Close-up view; the patient indicates the lesion is raised or bumpy; self-categorized by the patient as a rash; the contributor is a female aged 18–29; symptoms reported: pain, itching, darkening and bothersome appearance; no constitutional symptoms were reported; the condition has been present for one to four weeks; the affected area is the leg: 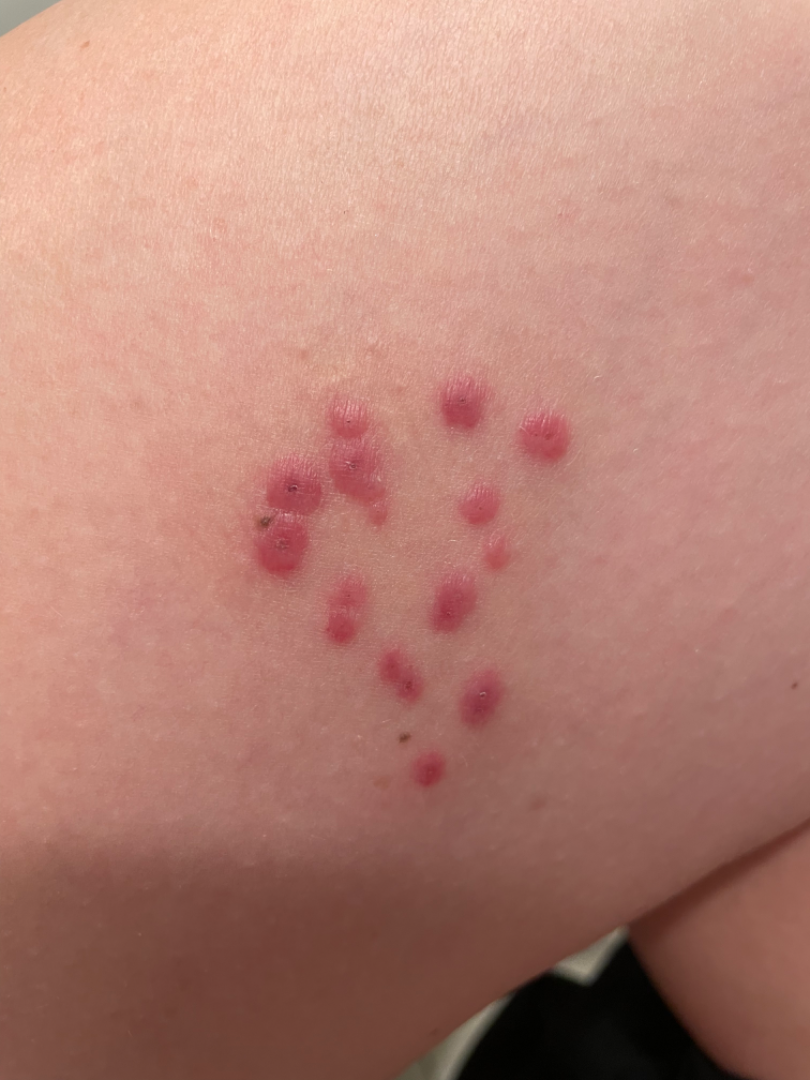On remote review of the image, the primary impression is Insect Bite; the differential also includes Herpes Zoster; less probable is Molluscum Contagiosum; less likely is Herpes Simplex; a remote consideration is Sweet syndrome.